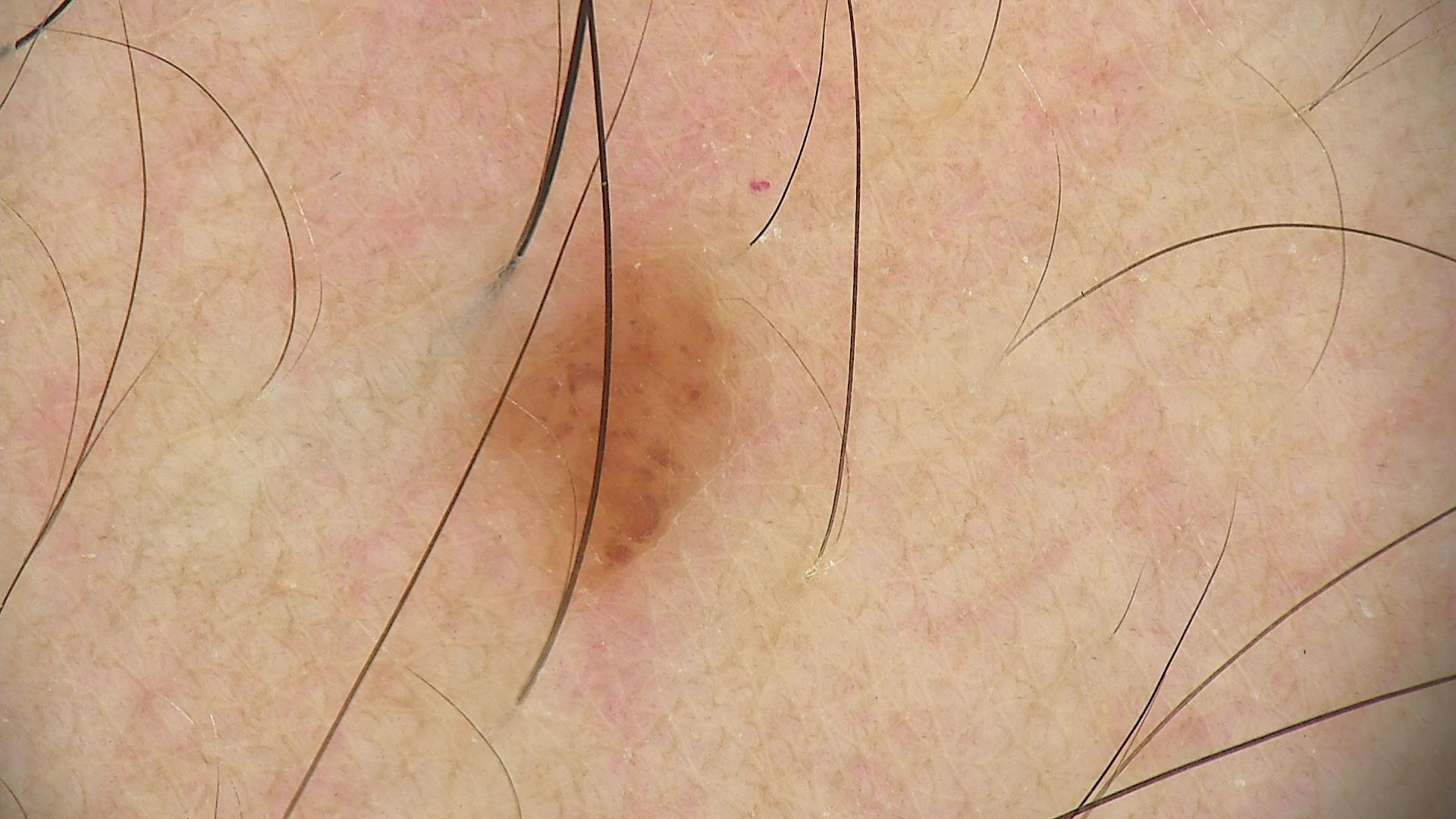Summary:
A dermoscopy image of a single skin lesion.
Conclusion:
The diagnosis was a banal lesion — a compound nevus.